A dermatoscopic image of a skin lesion:
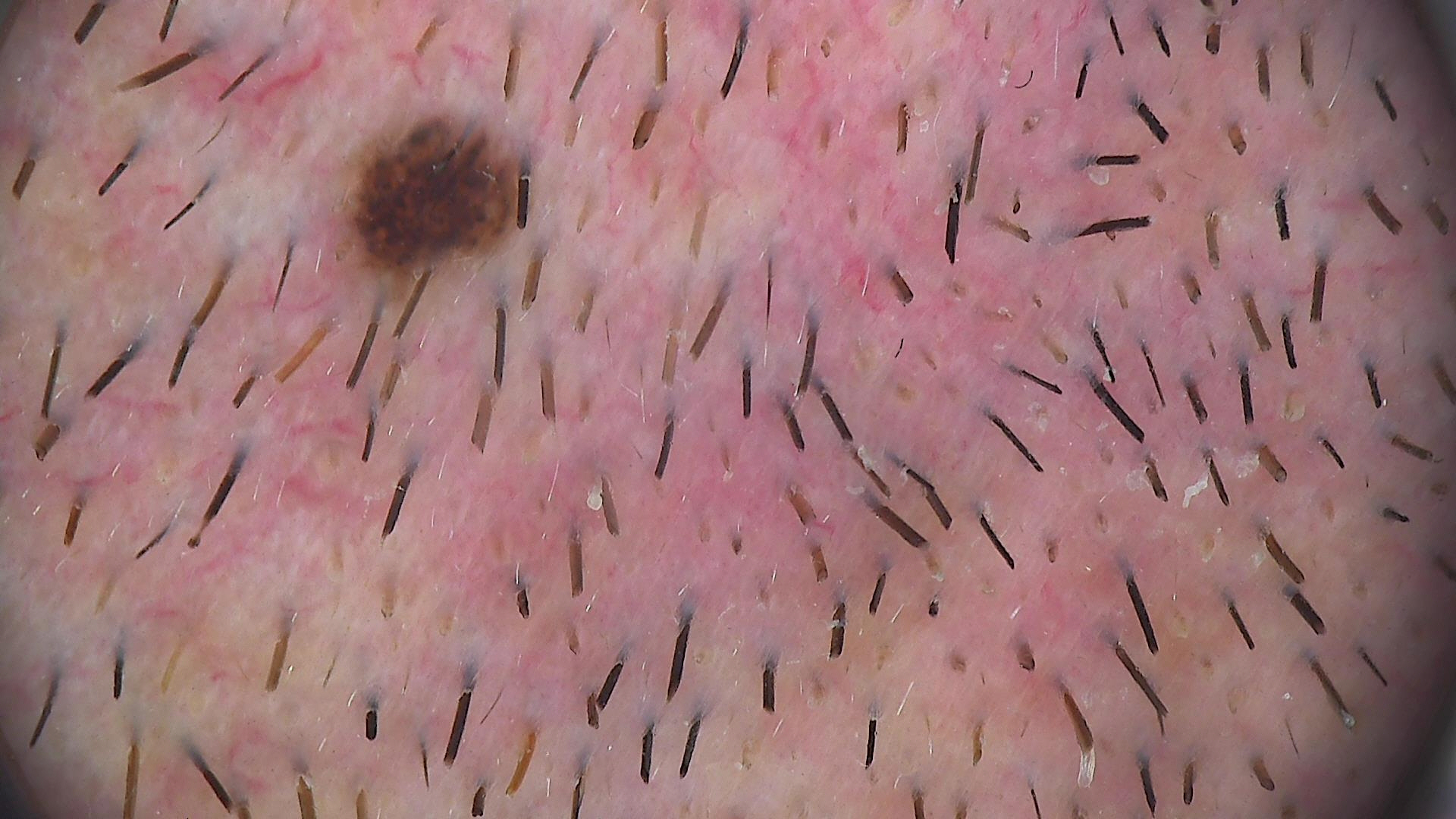Q: What was the diagnostic impression?
A: compound nevus (expert consensus)